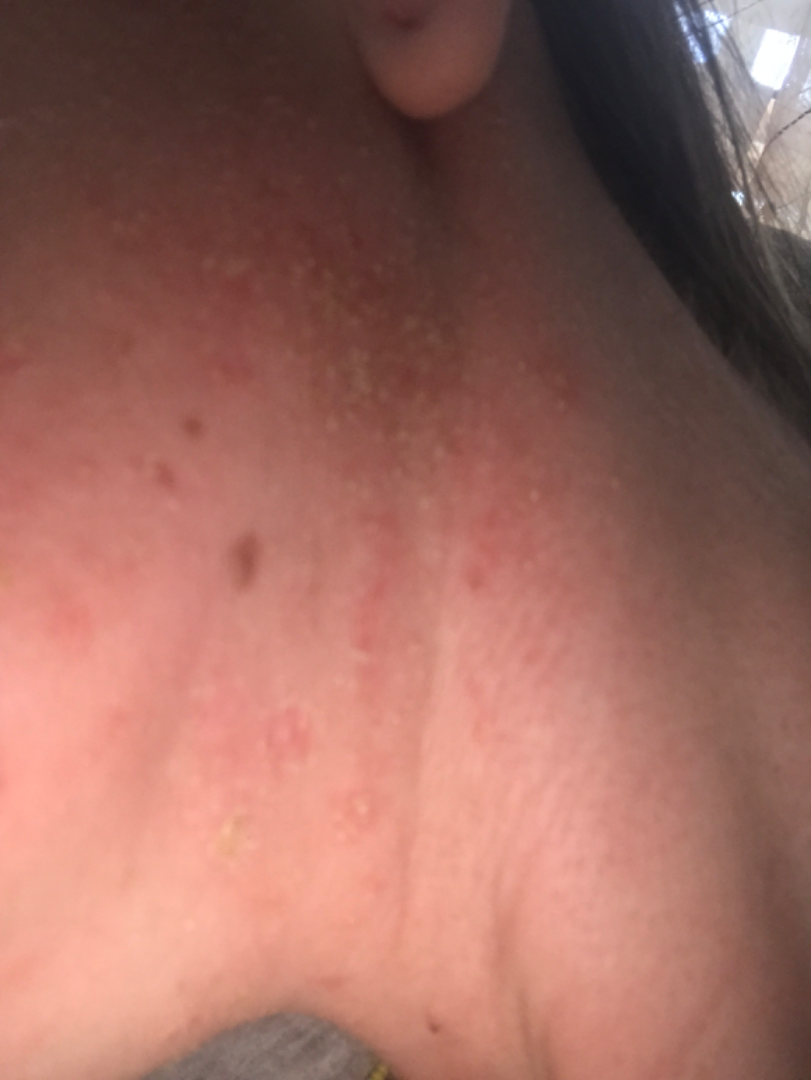Assessment: The case was indeterminate on photographic review.